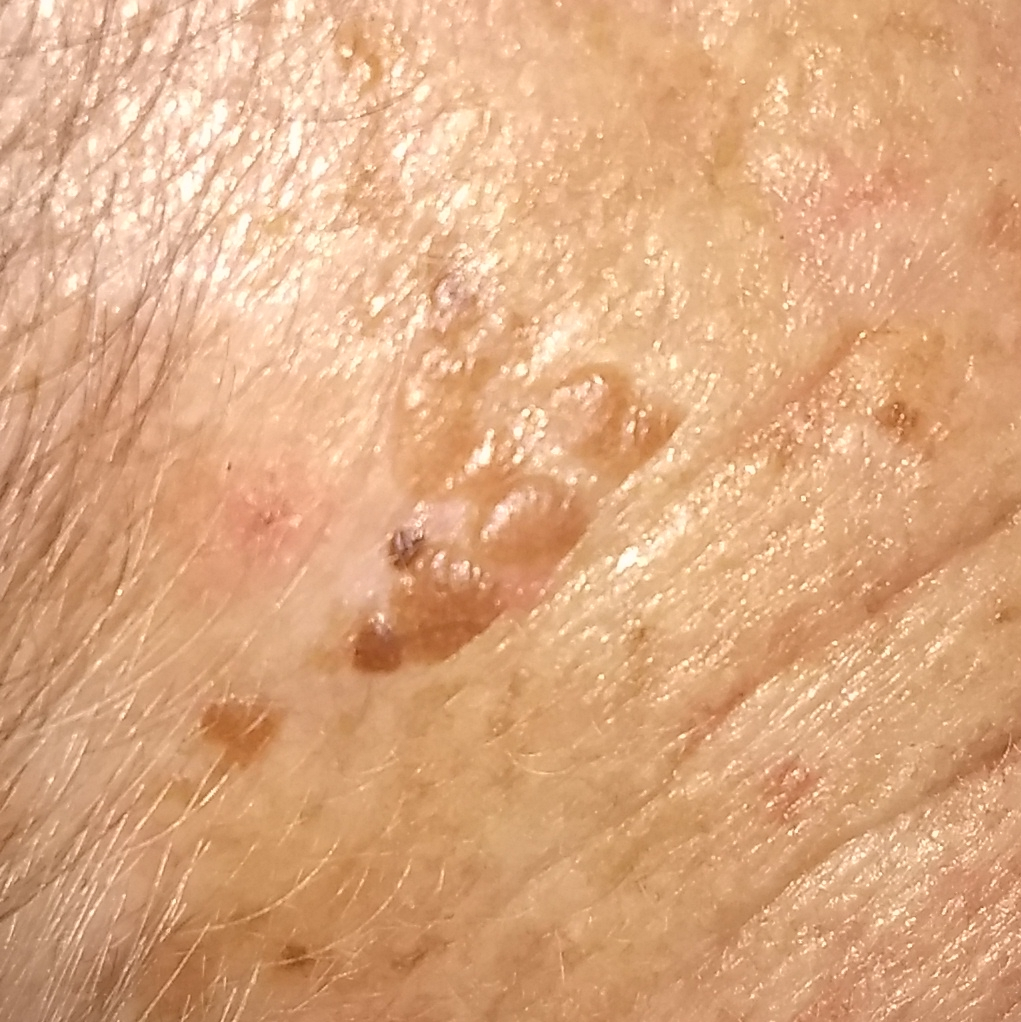Findings:
* subject · female, 77 years of age
* image · smartphone clinical photo
* region · the face
* patient-reported symptoms · elevation
* impression · seborrheic keratosis (clinical consensus)